The photo was captured at a distance. The lesion involves the leg:
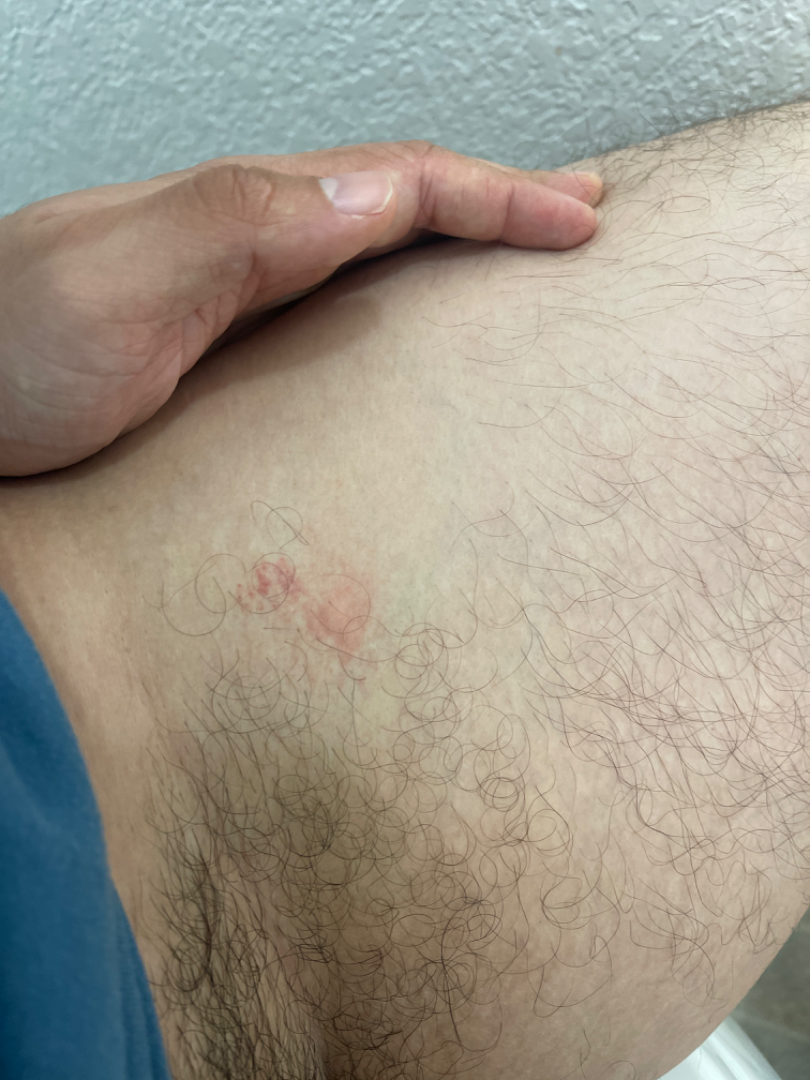lesion texture = raised or bumpy, skin tone = Fitzpatrick phototype III; lay reviewers estimated MST 2 or 3 (two reviewer pools), symptom duration = less than one week, differential diagnosis = the impression is Eczema.